A clinical photograph of a skin lesion · by self-report, a personal history of skin cancer · imaged for a research study, with no referral diagnosis recorded · a female patient 50 years of age · the patient says their skin reddens with sun exposure · a moderate number of moles by the patient's own estimate.
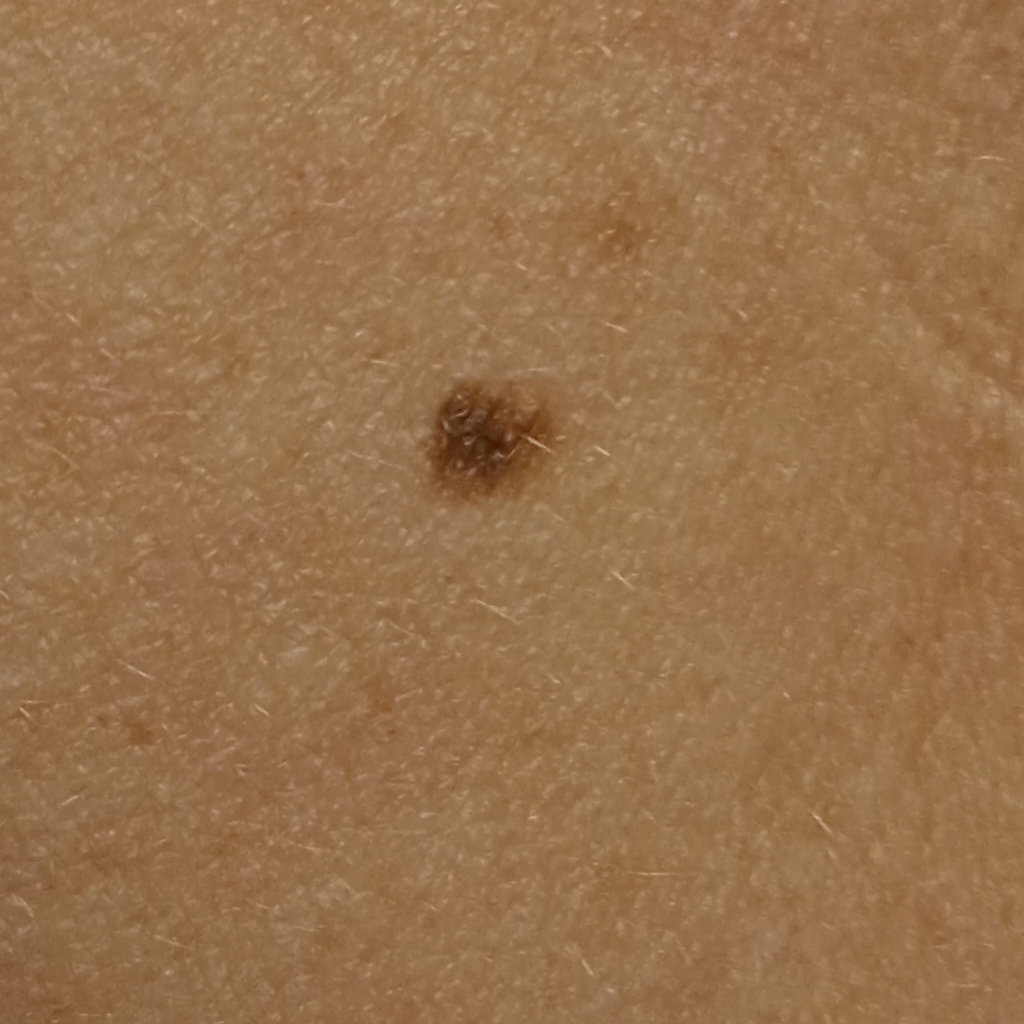Located on the torso. Measuring roughly 5.4 mm. The diagnostic impression was a melanocytic nevus.